The lesion is associated with itching; close-up view; male patient, age 18–29; the leg is involved; present for about one day; the patient reported no systemic symptoms; self-categorized by the patient as a rash.
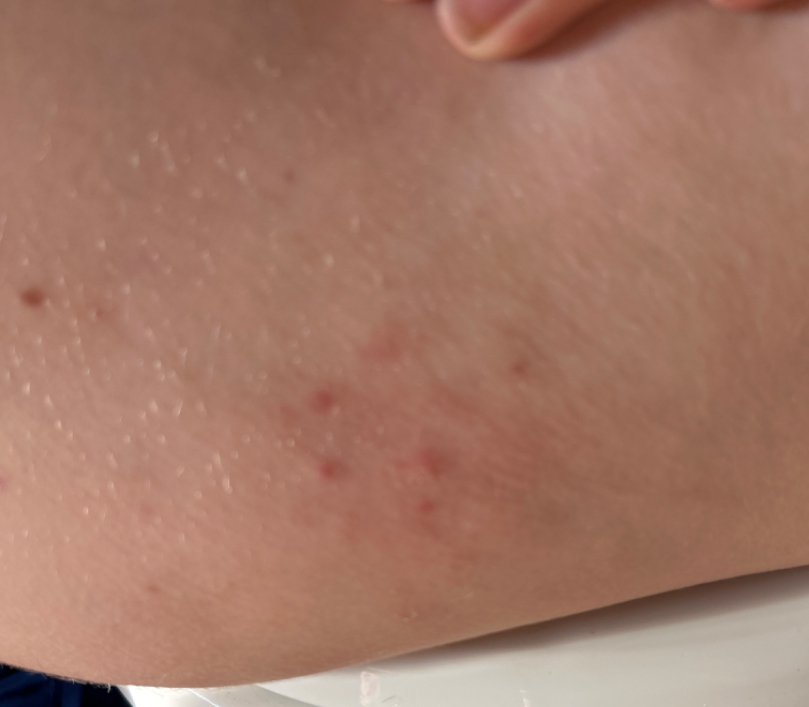Q: What was the assessment?
A: indeterminate